The patient considered this skin that appeared healthy to them; the patient reports the condition has been present for one to four weeks; the photograph is a close-up of the affected area; texture is reported as raised or bumpy; reported lesion symptoms include itching; the contributor is 30–39, male; the affected area is the arm:
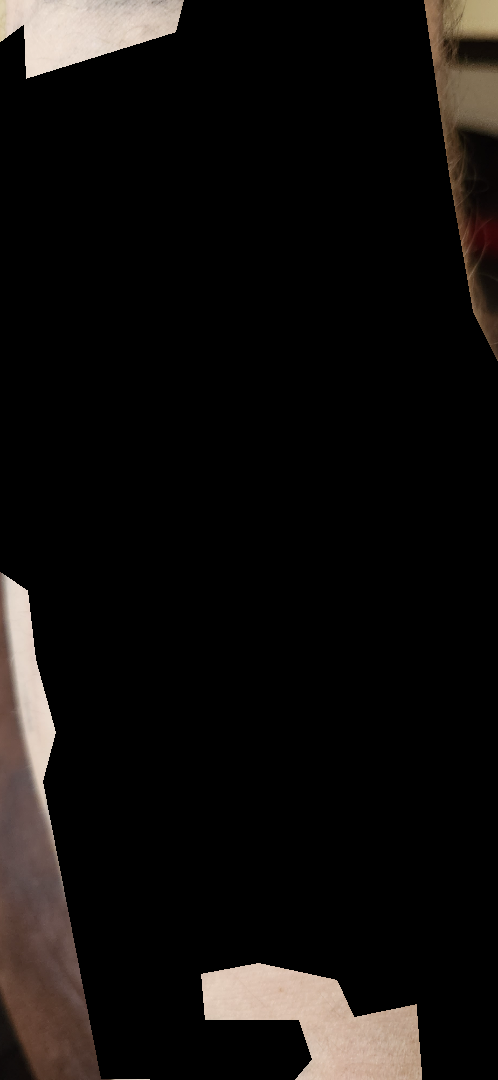assessment=indeterminate from the photograph.